Dermoscopy of a skin lesion:
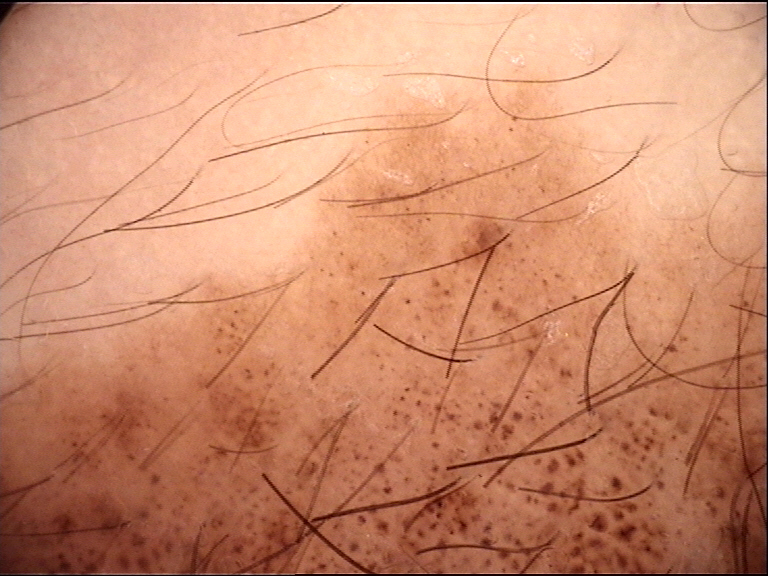{
  "diagnosis": {
    "name": "congenital compound nevus",
    "code": "ccb",
    "malignancy": "benign",
    "super_class": "melanocytic",
    "confirmation": "expert consensus"
  }
}